A dermoscopic photograph of a skin lesion.
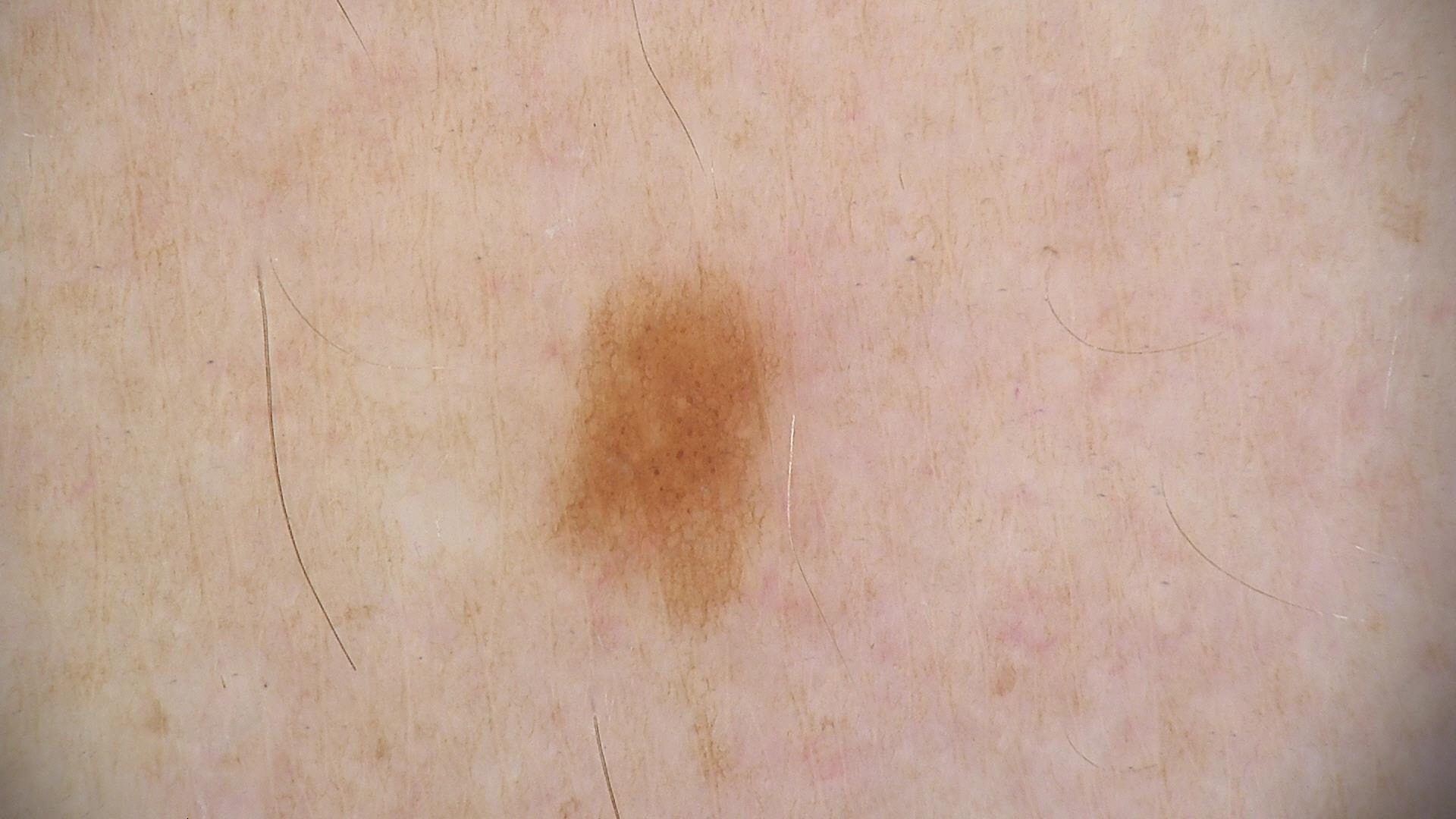• assessment · dysplastic junctional nevus (expert consensus)